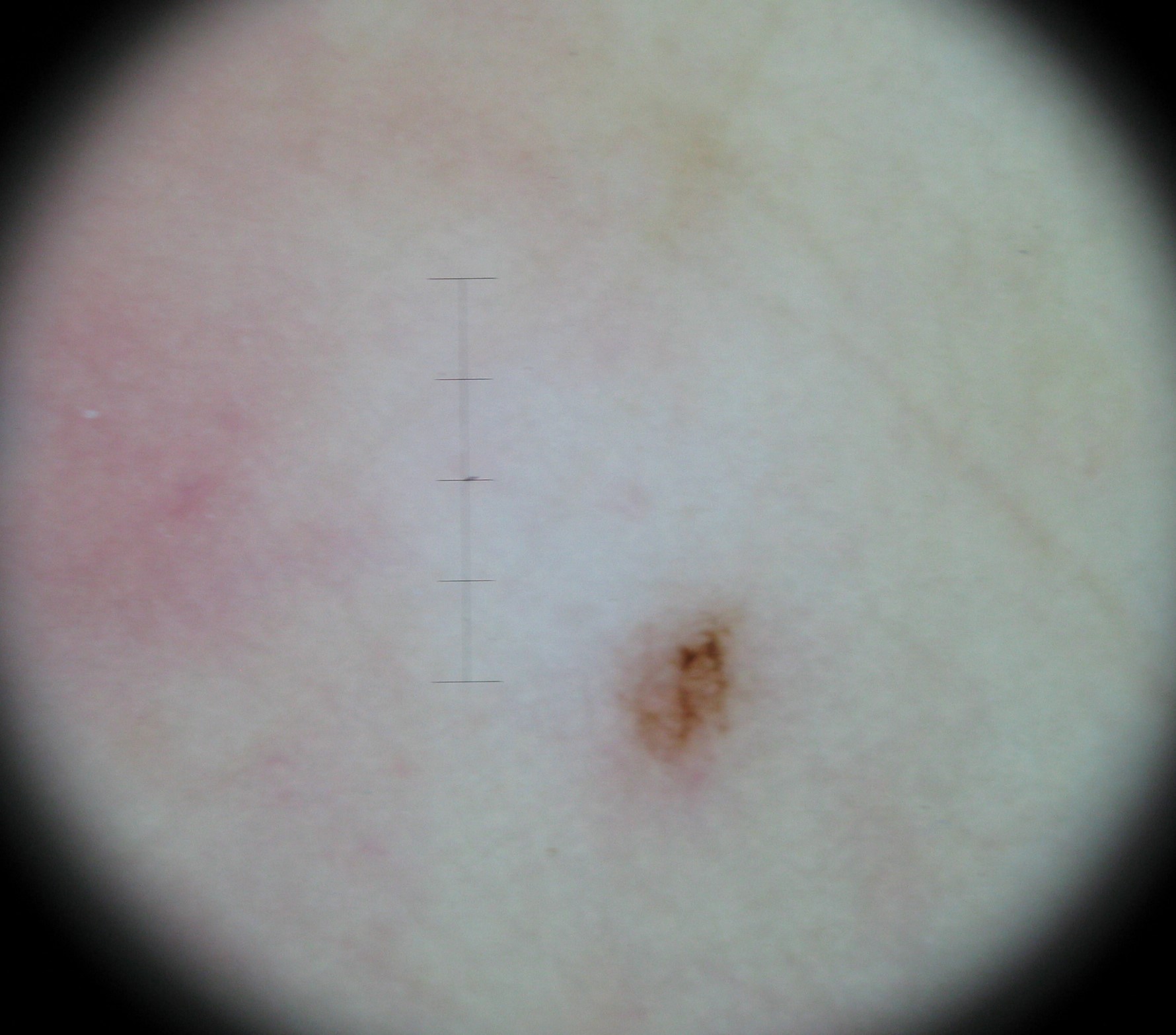imaging — dermoscopy; class — acral dysplastic junctional nevus (expert consensus).